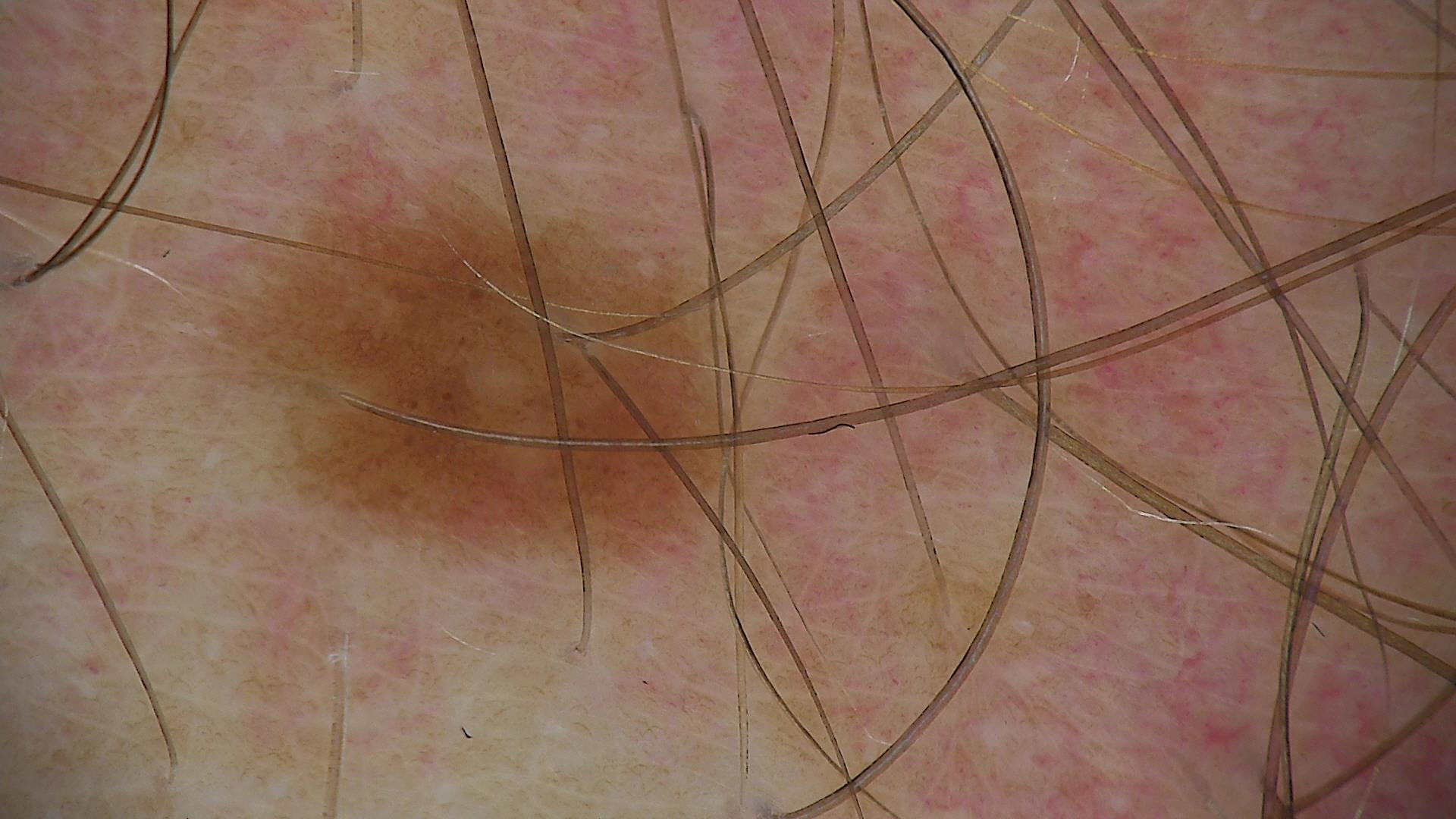image = dermoscopy; diagnosis = dysplastic junctional nevus (expert consensus).